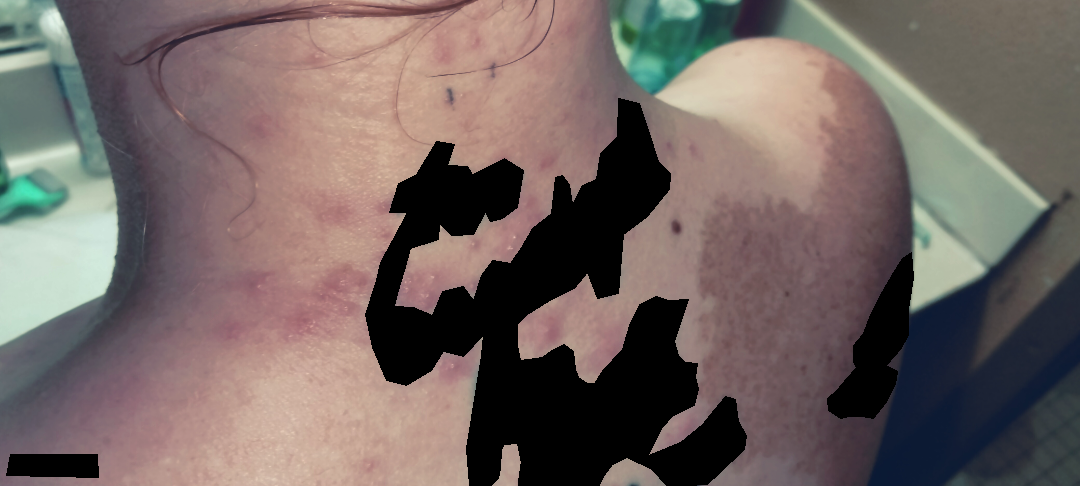The photograph is a close-up of the affected area.
The condition has been present for less than one week.
The lesion involves the front of the torso, head or neck and back of the torso.
The contributor is a female aged 18–29.
On remote review of the image, favoring Acne; an alternative is Folliculitis; less likely is Allergic Contact Dermatitis.